A dermoscopic photograph of a skin lesion.
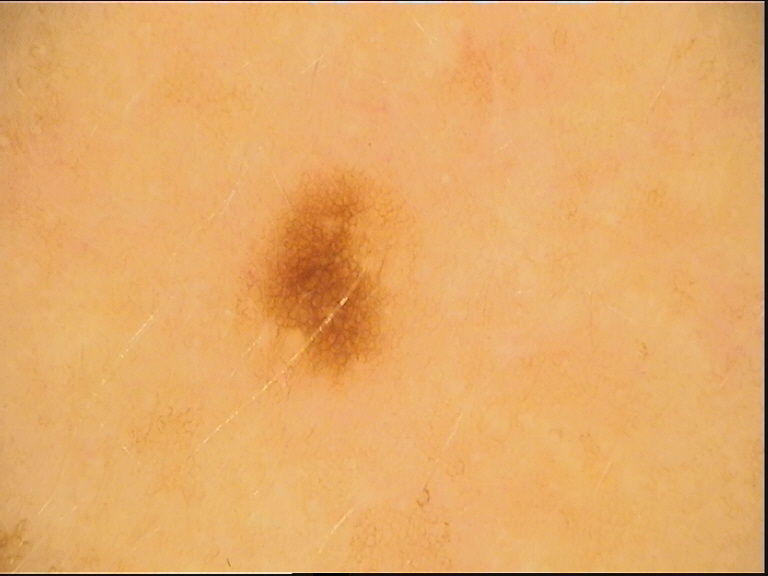The diagnostic label was a junctional nevus.